A dermoscopic close-up of a skin lesion.
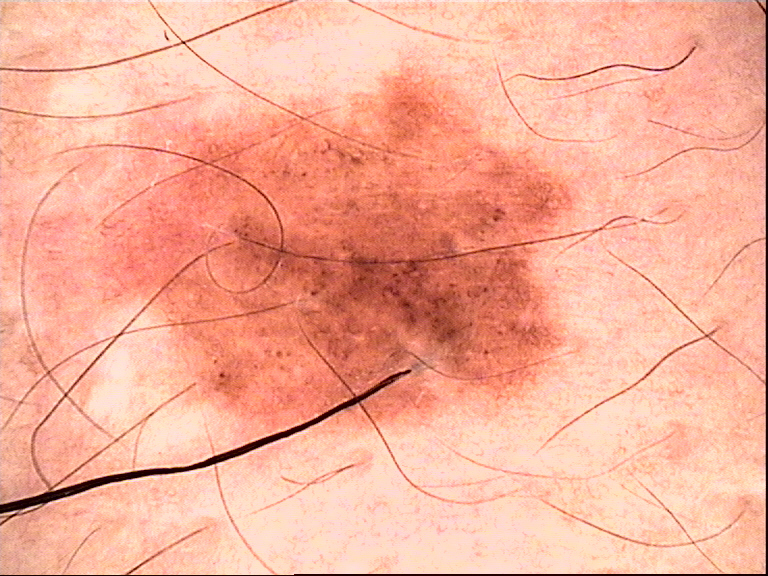label: dysplastic compound nevus (expert consensus).